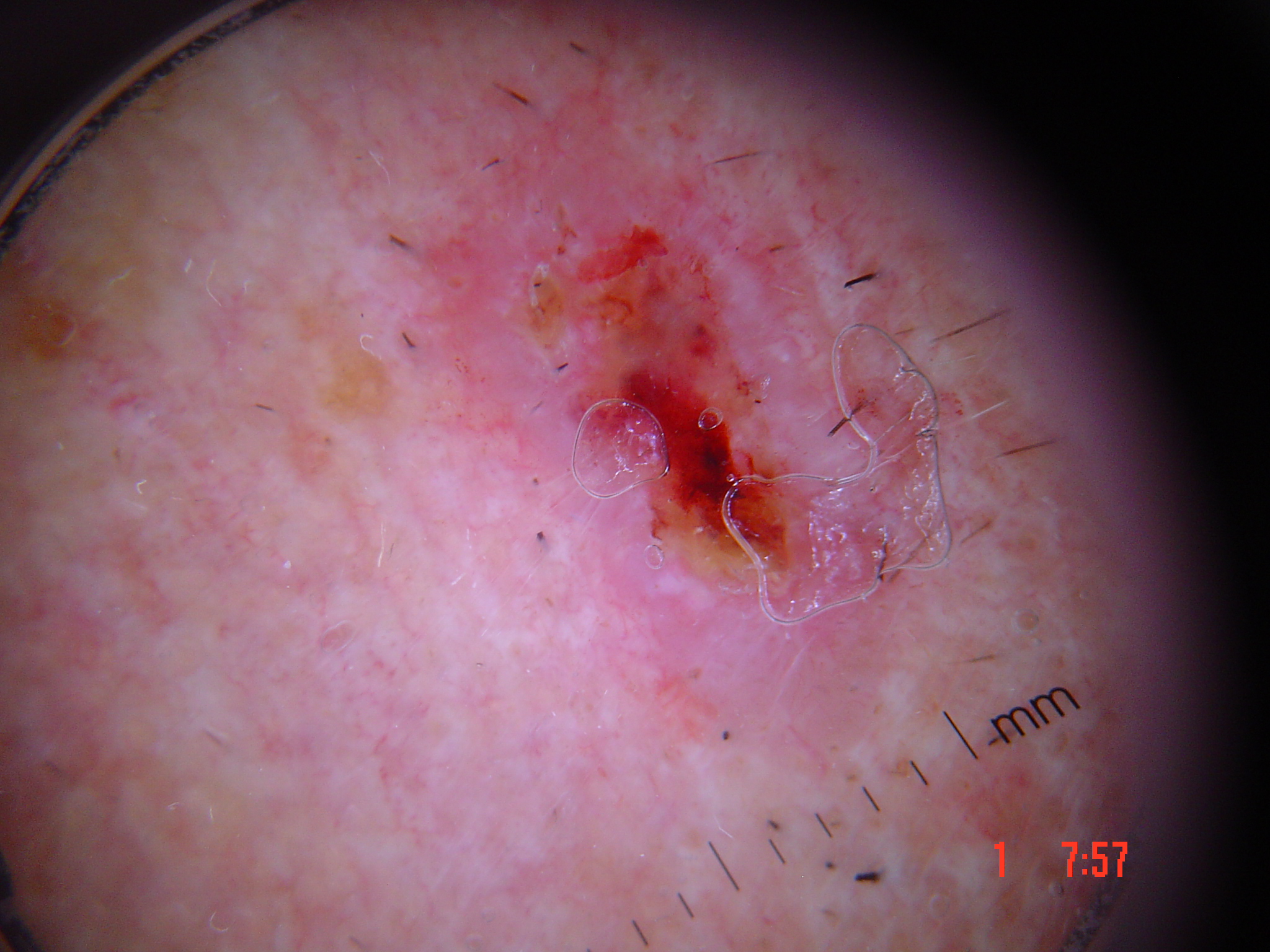A skin lesion imaged with a dermatoscope. This is a keratinocytic lesion. Biopsy-confirmed as a malignant lesion — a squamous cell carcinoma.